The lesion involves the arm · the photograph is a close-up of the affected area · the contributor is a female aged 40–49 — 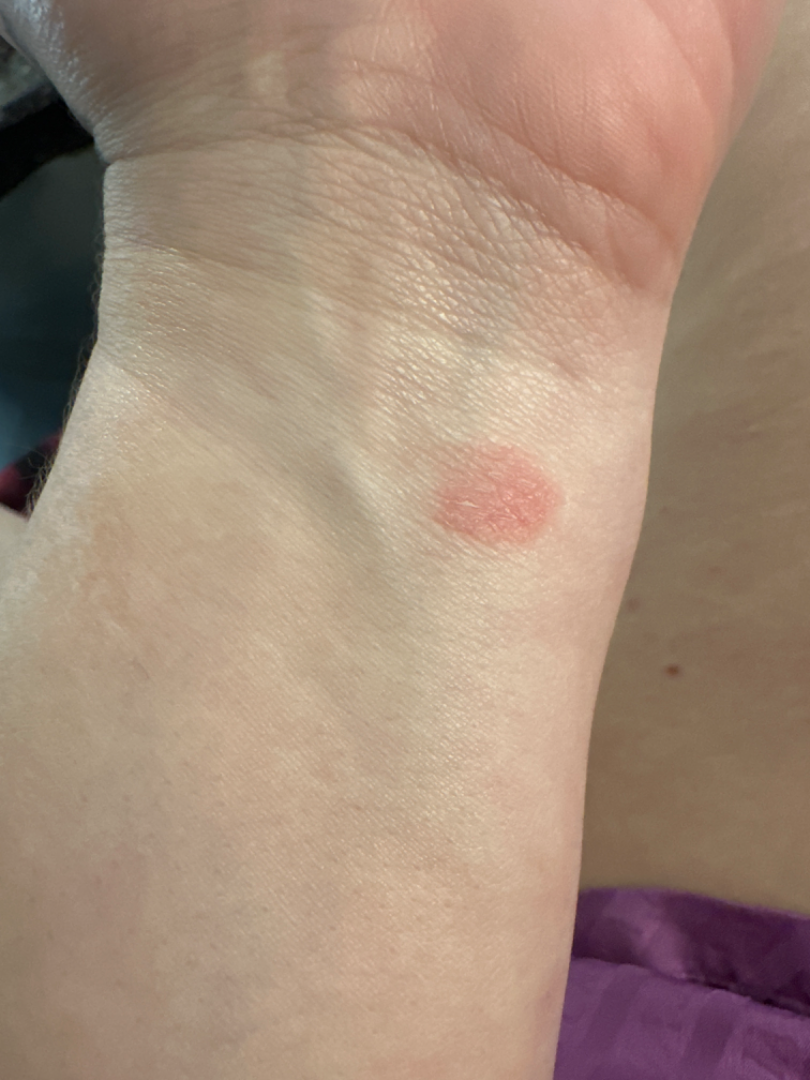| feature | finding |
|---|---|
| differential diagnosis | Eczema and Allergic Contact Dermatitis were each considered, in no particular order |